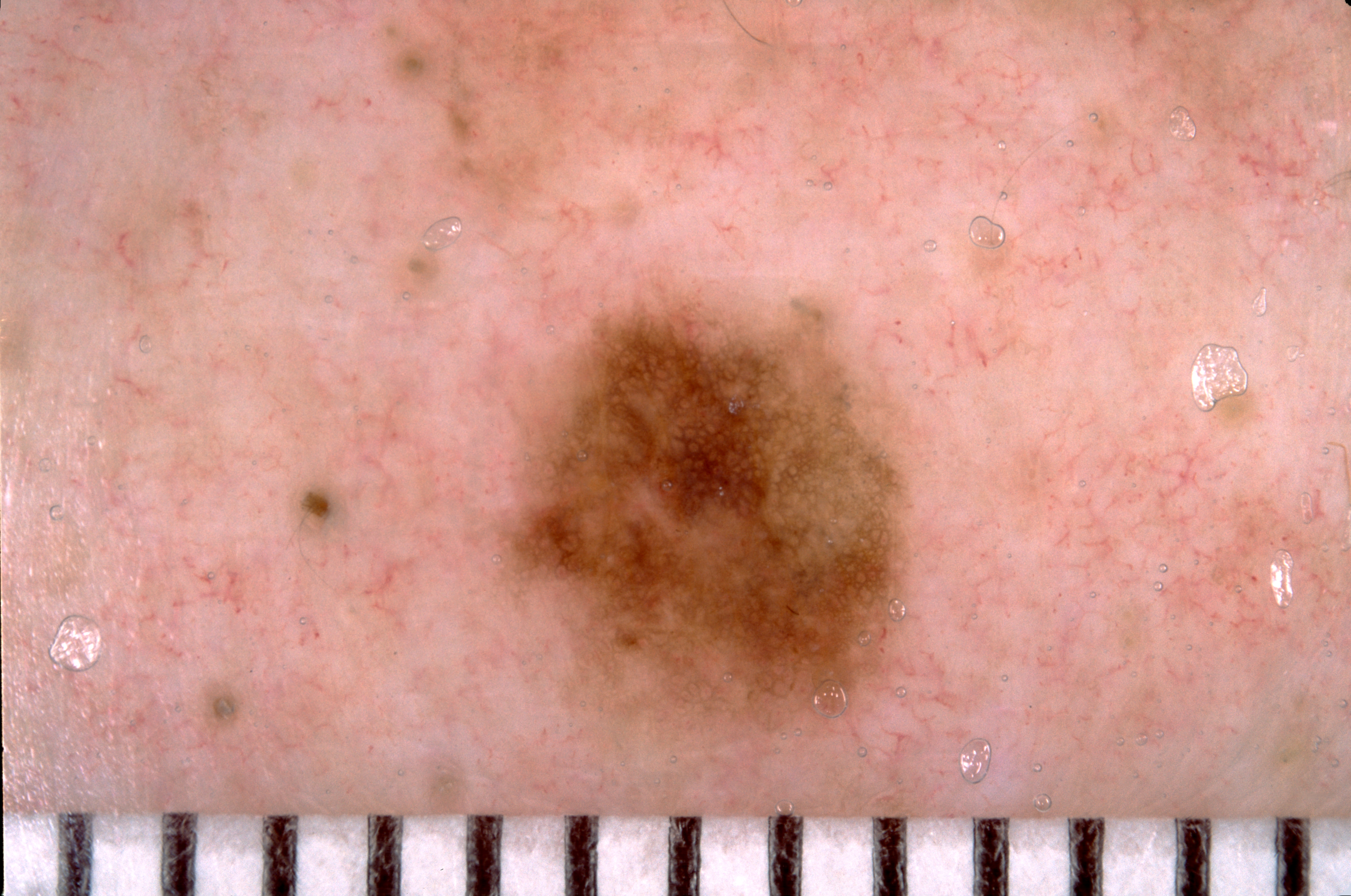| feature | finding |
|---|---|
| image type | dermoscopy of a skin lesion |
| lesion bbox | [488, 282, 913, 785] |
| dermoscopic pattern | pigment network; absent: negative network, streaks, and milia-like cysts |
| assessment | a melanocytic nevus |